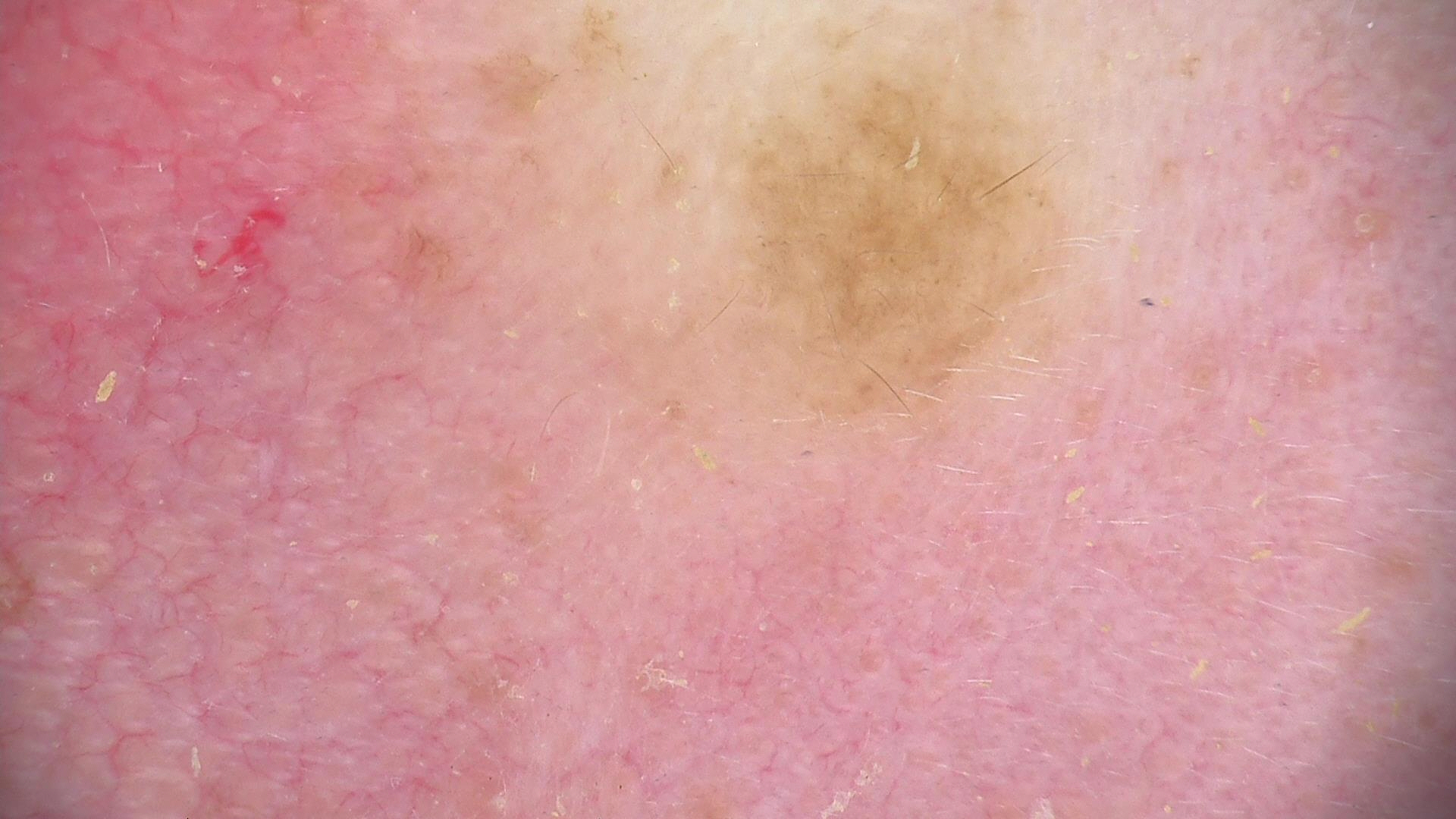| feature | finding |
|---|---|
| label | compound nevus (expert consensus) |